Imaged for a research study, with no referral diagnosis recorded. A male subject aged 62. A macroscopic clinical photograph of a skin lesion — 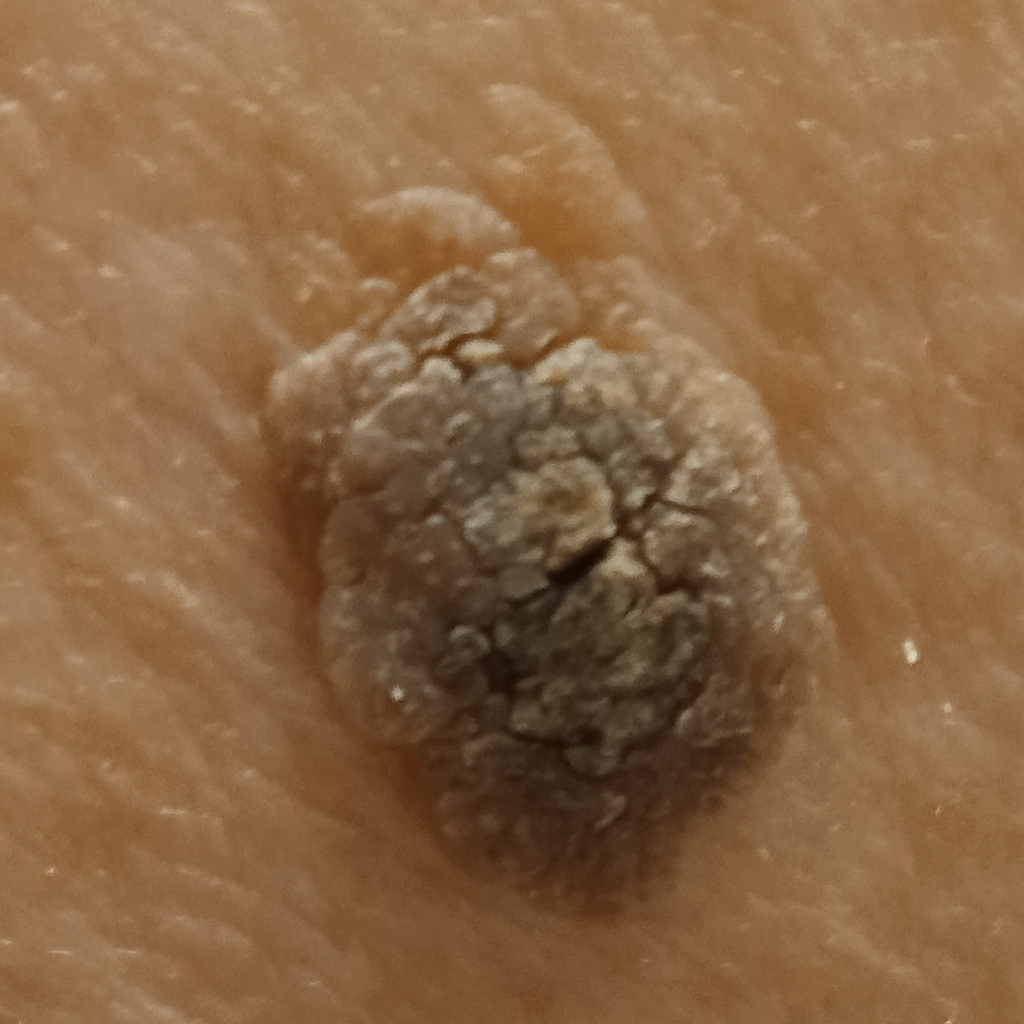Findings:
- location — the back
- size — 10.9 mm
- assessment — seborrheic keratosis (dermatologist consensus)